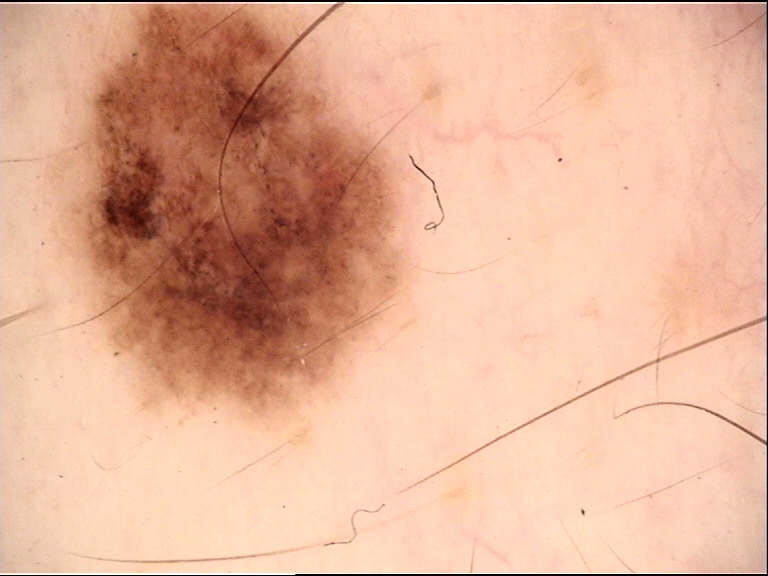Labeled as a benign lesion — a dysplastic junctional nevus.